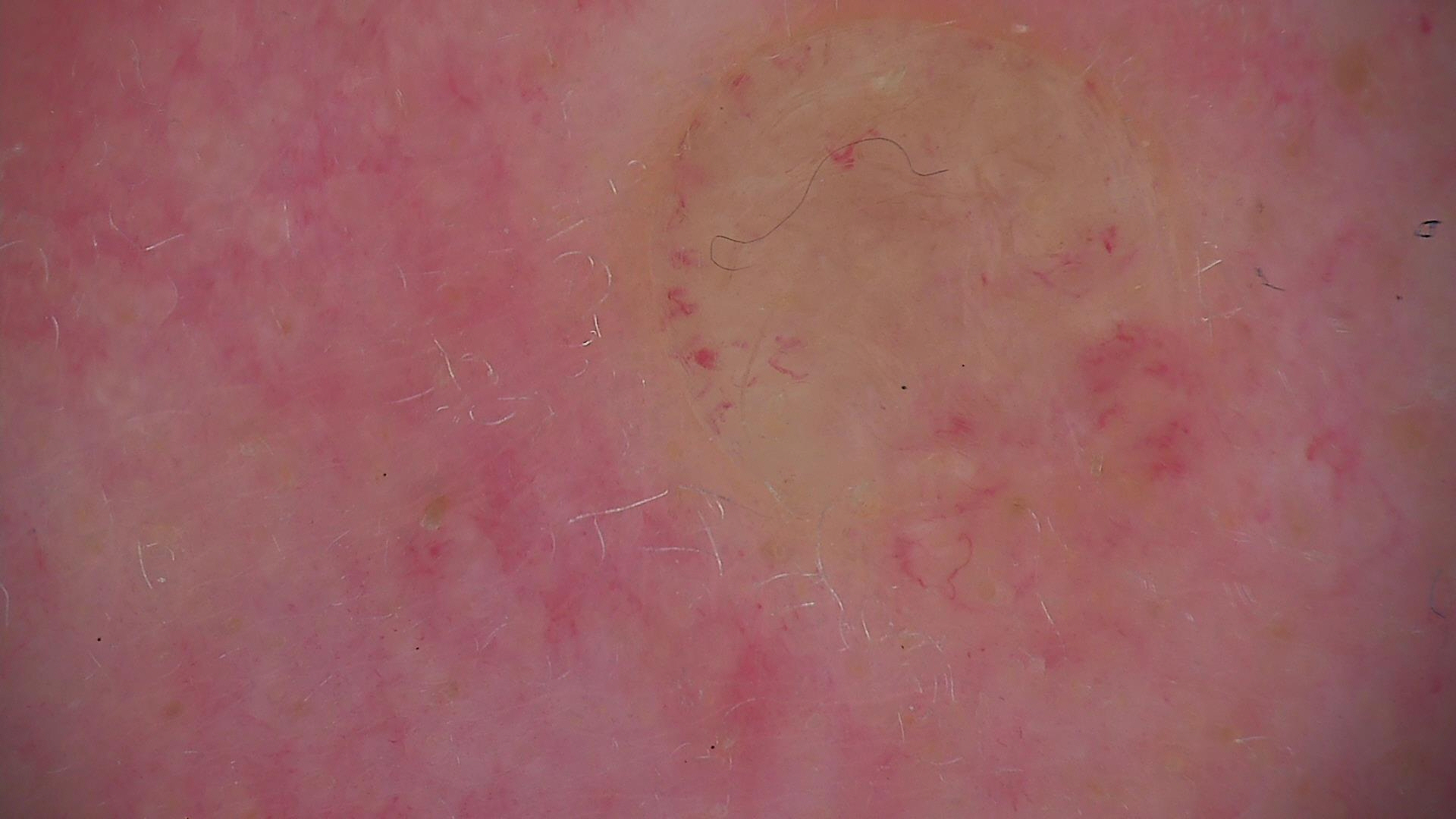A dermoscopy image of a single skin lesion. The morphology is that of a banal lesion. Diagnosed as a dermal nevus.